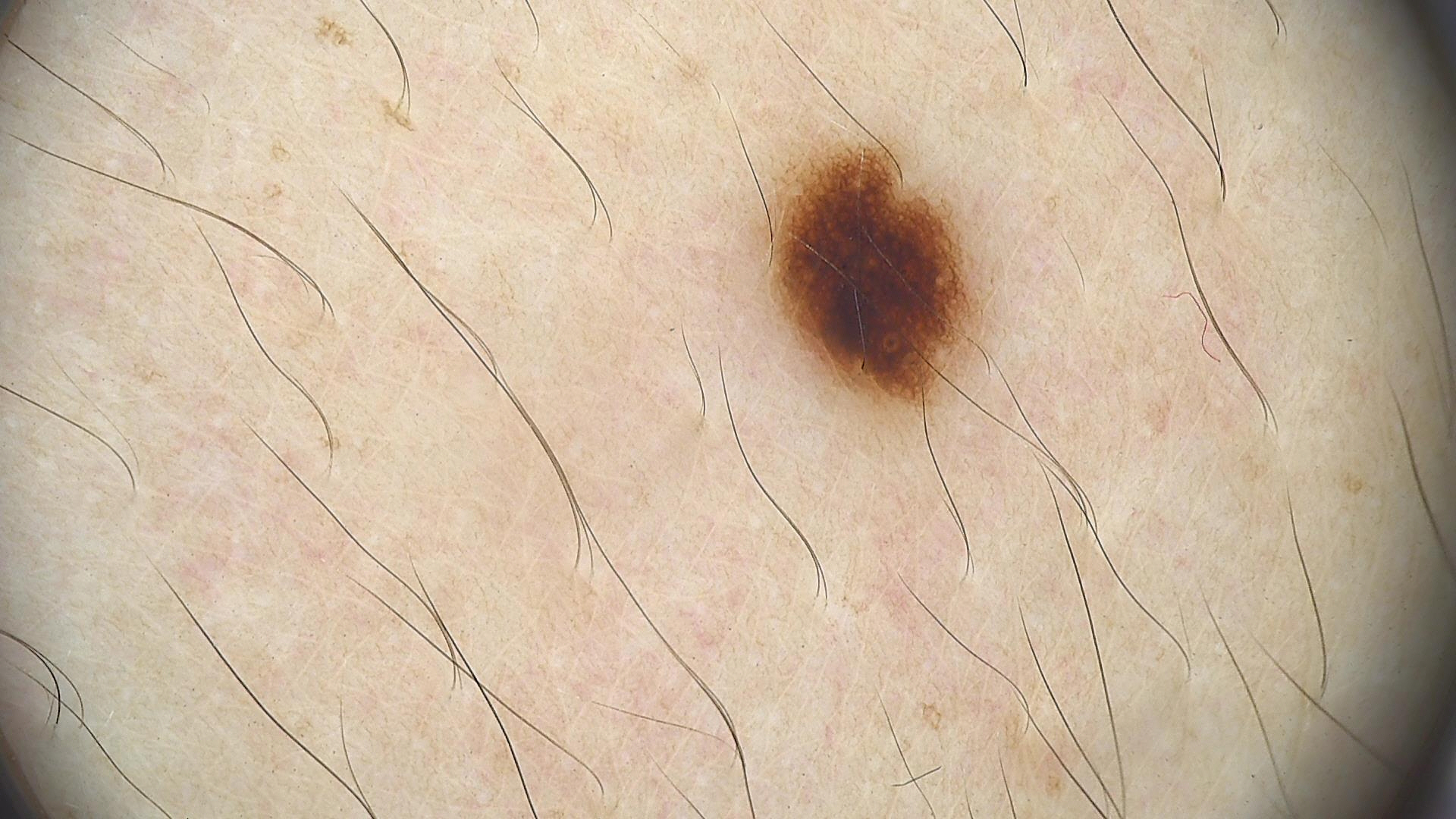{"image": "dermatoscopy", "diagnosis": {"name": "dysplastic junctional nevus", "code": "jd", "malignancy": "benign", "super_class": "melanocytic", "confirmation": "expert consensus"}}